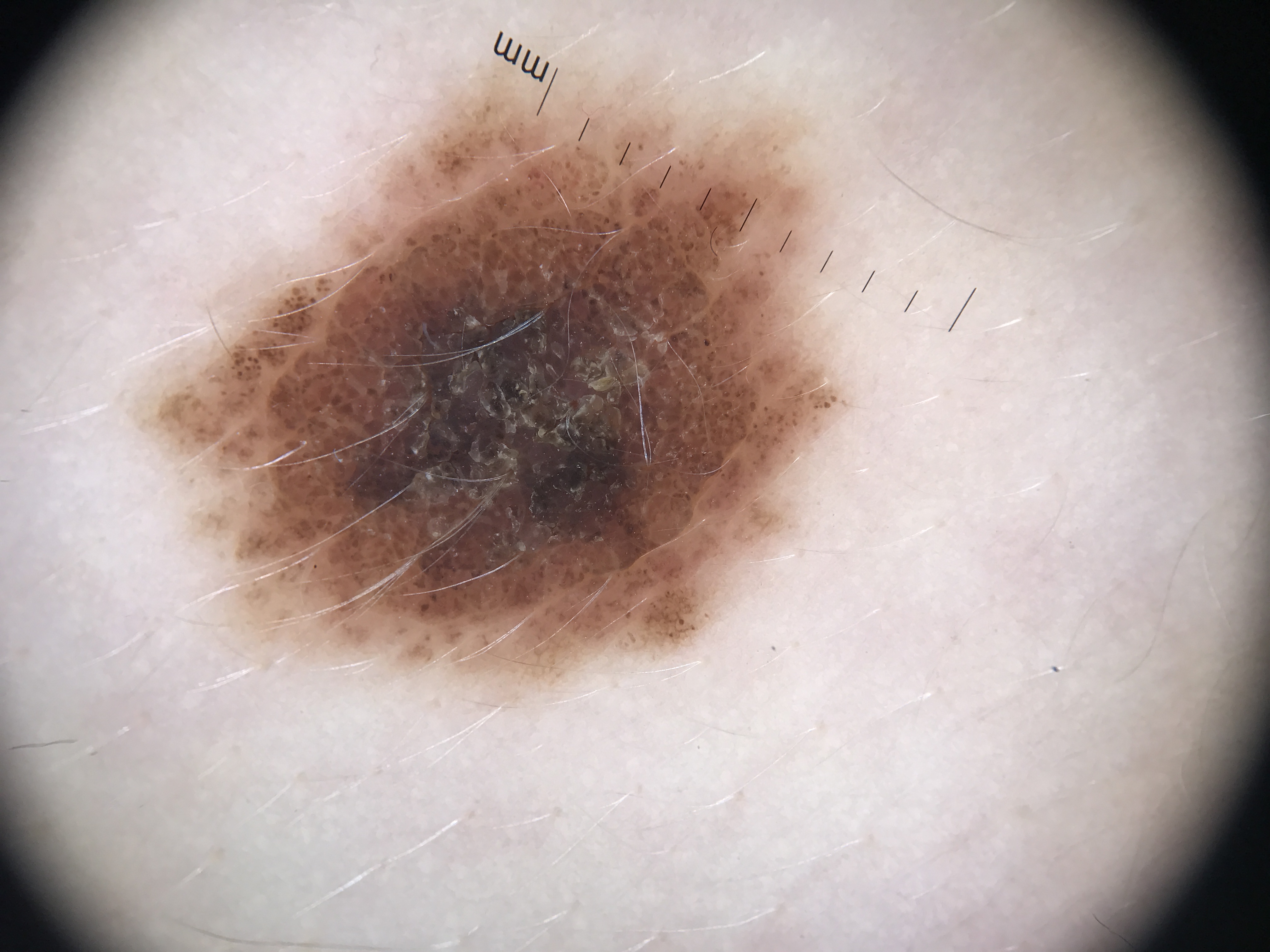- imaging: dermoscopy
- diagnosis: dysplastic compound nevus (expert consensus)